The photo was captured at a distance, the condition has been present for about one day, the contributor is a female aged 30–39, no relevant lesion symptoms reported, the patient considered this skin that appeared healthy to them, located on the leg, the lesion is described as flat:
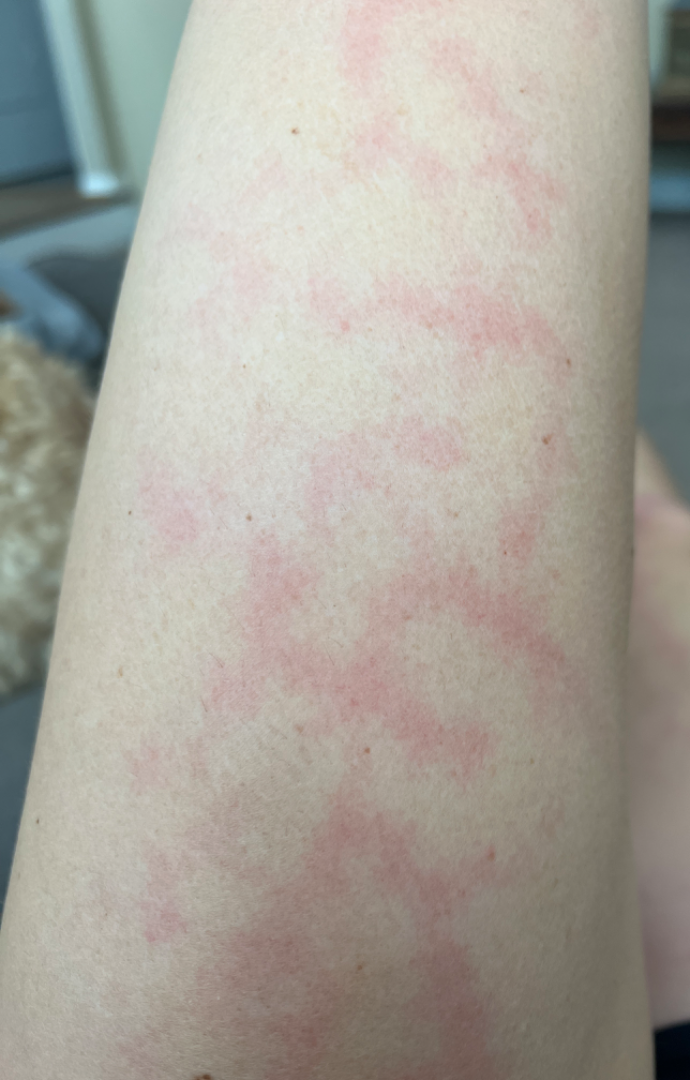  differential:
    leading:
      - Livedo reticularis
    considered:
      - Erythema ab igne